A skin lesion imaged with a dermatoscope.
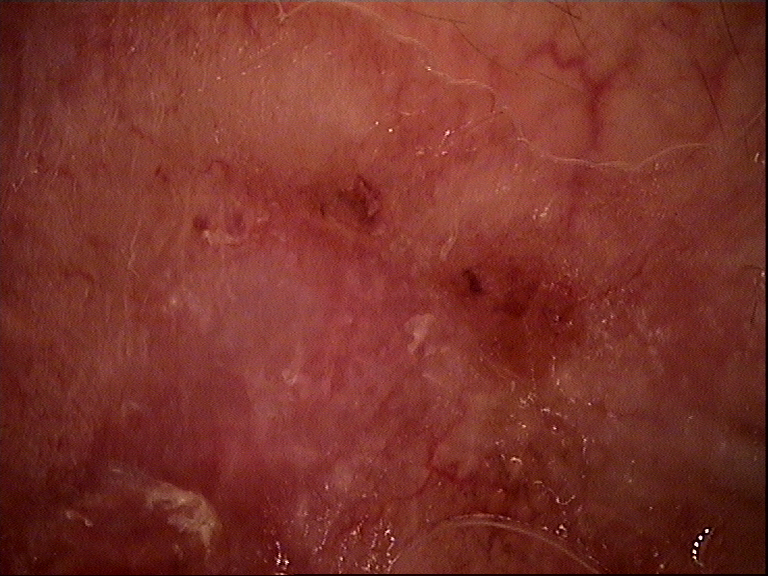This is a keratinocytic lesion. Confirmed on histopathology as a basal cell carcinoma.